This image was taken at a distance.
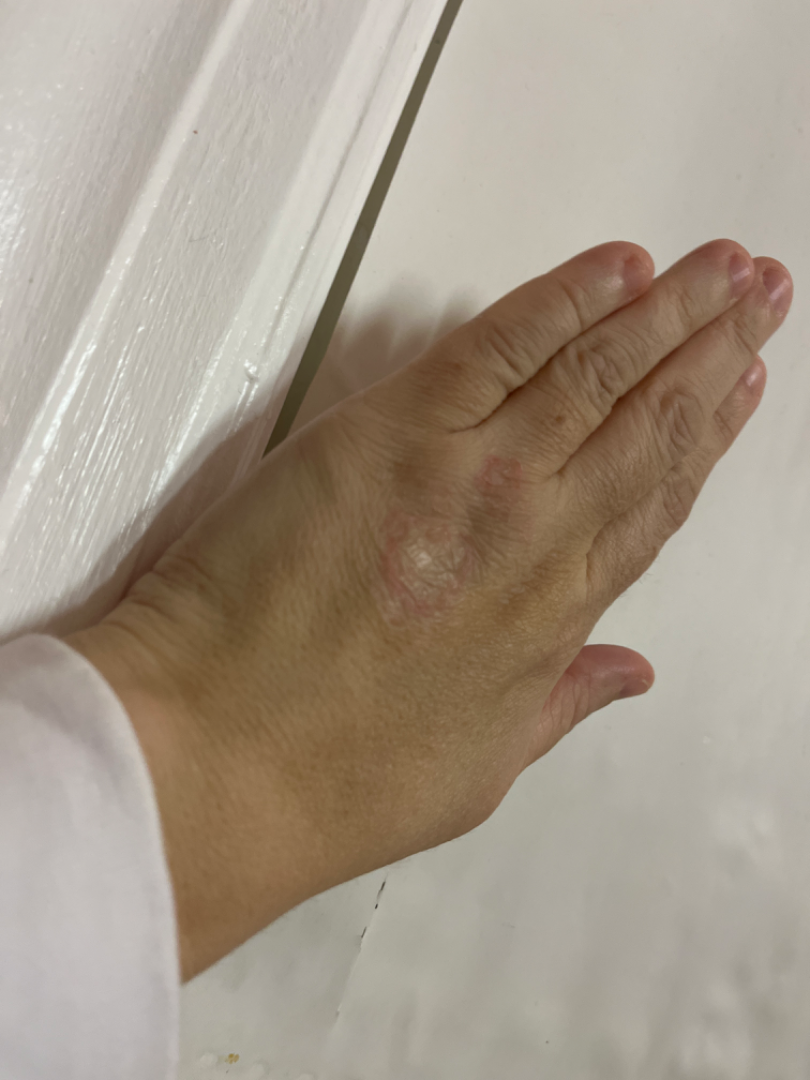| feature | finding |
|---|---|
| impression | Tinea (considered); Eczema (considered) |